Located on the head or neck, close-up view:
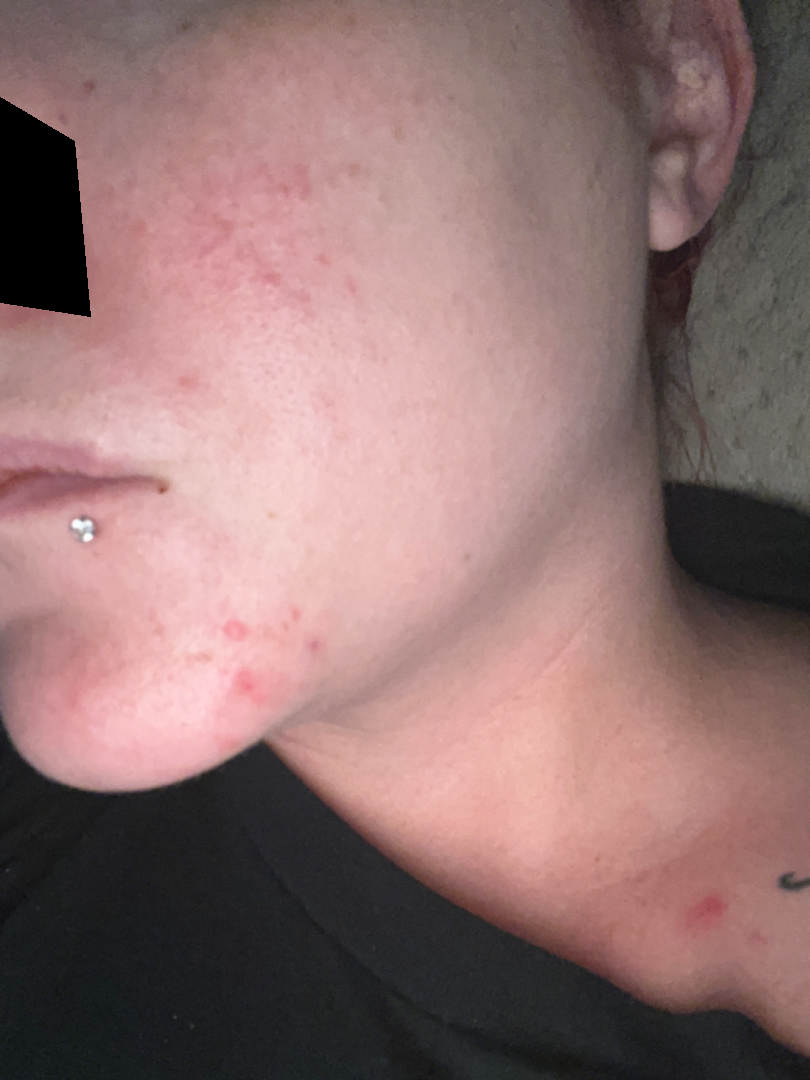The skin findings could not be characterized from the image. The condition has been present for one to three months. The patient indicates the lesion is raised or bumpy. The patient indicates enlargement. Fitzpatrick phototype II. The patient considered this acne. No relevant systemic symptoms.